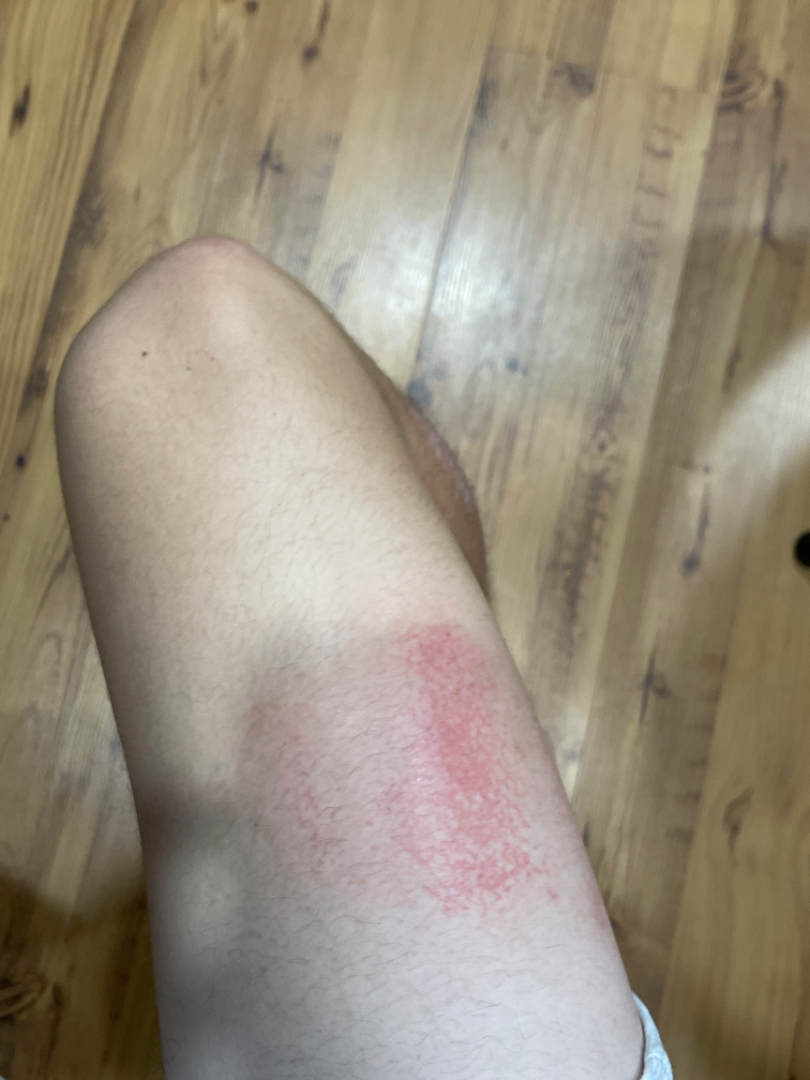Present for less than one week.
The patient considered this a rash.
The contributor is a male aged 18–29.
Symptoms reported: burning, bothersome appearance and pain.
The patient notes the lesion is rough or flaky.
The lesion involves the leg.
This image was taken at a distance.
Most likely Eczema; less likely is Erythema ab igne; less probable is Livedoid vasculopathy.